The patient is a male aged 40–49 · skin tone: Fitzpatrick phototype V; lay graders estimated Monk skin tone scale 7 (US pool) or 4 (India pool) · this image was taken at an angle · the lesion involves the top or side of the foot · the contributor notes the condition has been present for more than one year · texture is reported as rough or flaky, raised or bumpy and fluid-filled: 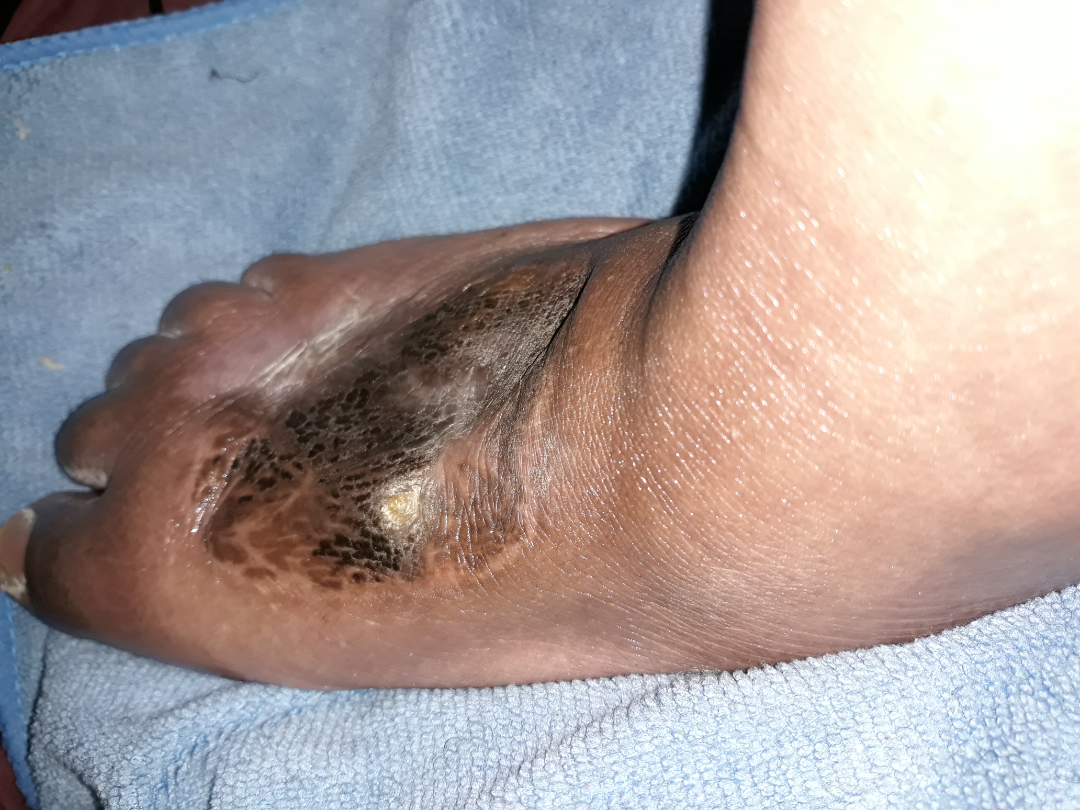| key | value |
|---|---|
| diagnostic considerations | favoring Foot ulcer; also raised was Mixed diabetic ulcer - foot; also consider Deep fungal infection |